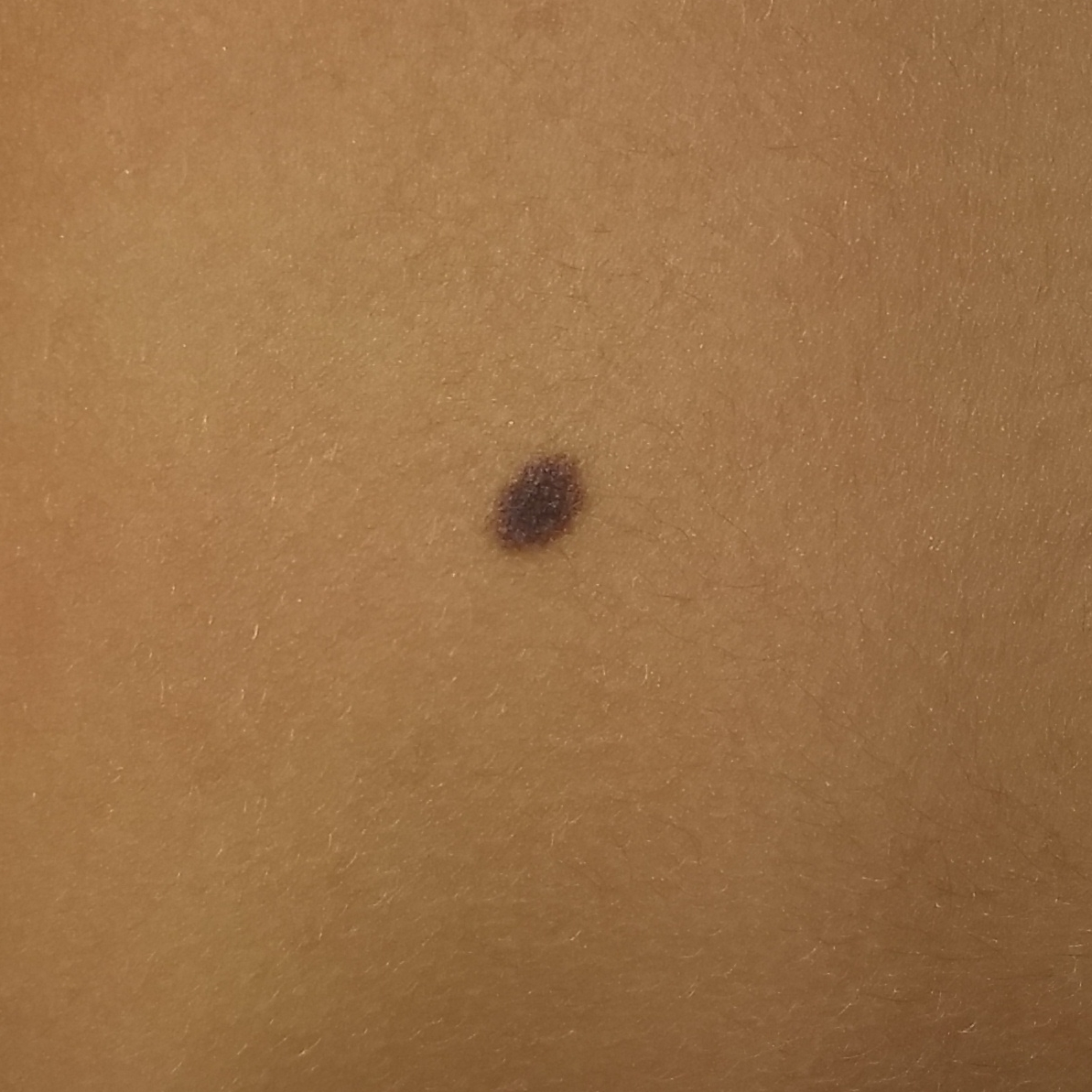Clinical context: A clinical photograph showing a skin lesion. Asymptomatic by report. Impression: Expert review favored a nevus.